A dermoscopic close-up of a skin lesion.
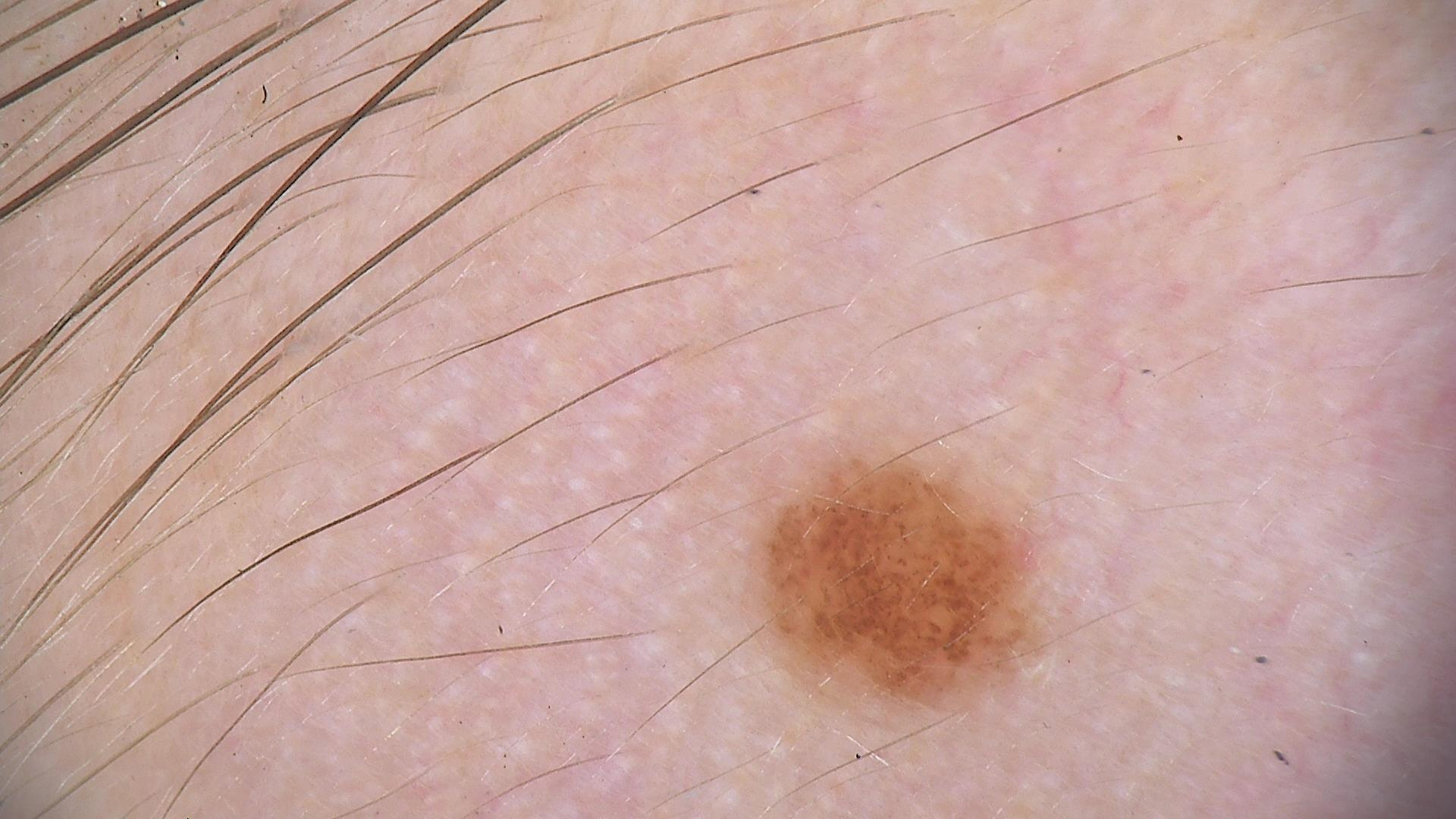Consistent with a benign lesion — a dysplastic junctional nevus.